A dermoscopic image of a skin lesion.
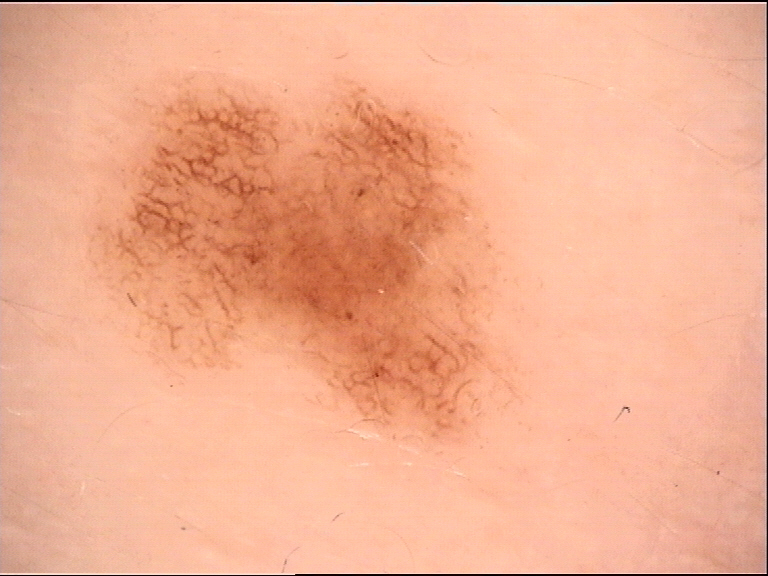Impression: The diagnosis was a dysplastic junctional nevus.